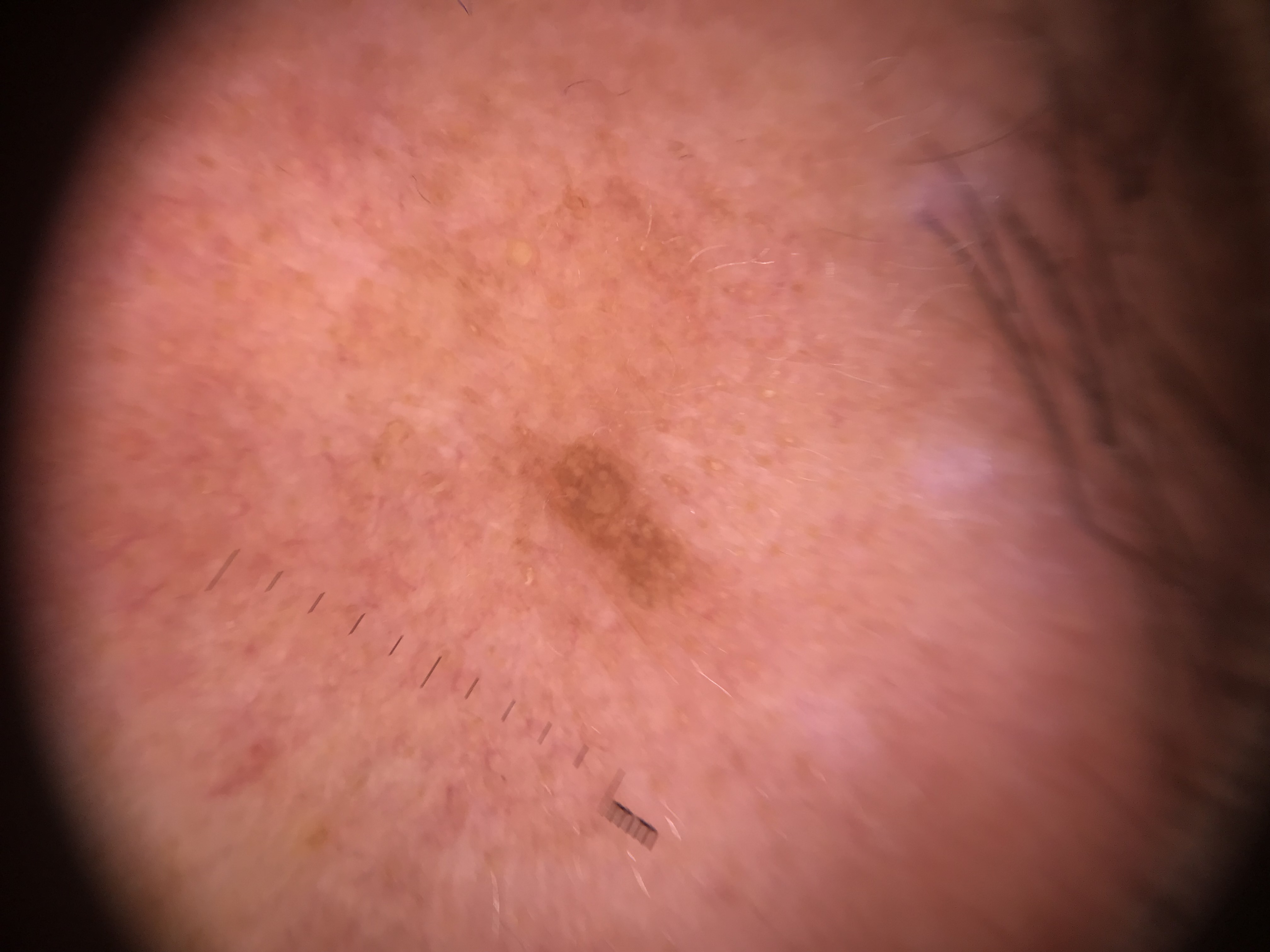A dermatoscopic image of a skin lesion. The morphology is that of a keratinocytic lesion. Labeled as a seborrheic keratosis.